A dermoscopic image of a skin lesion:
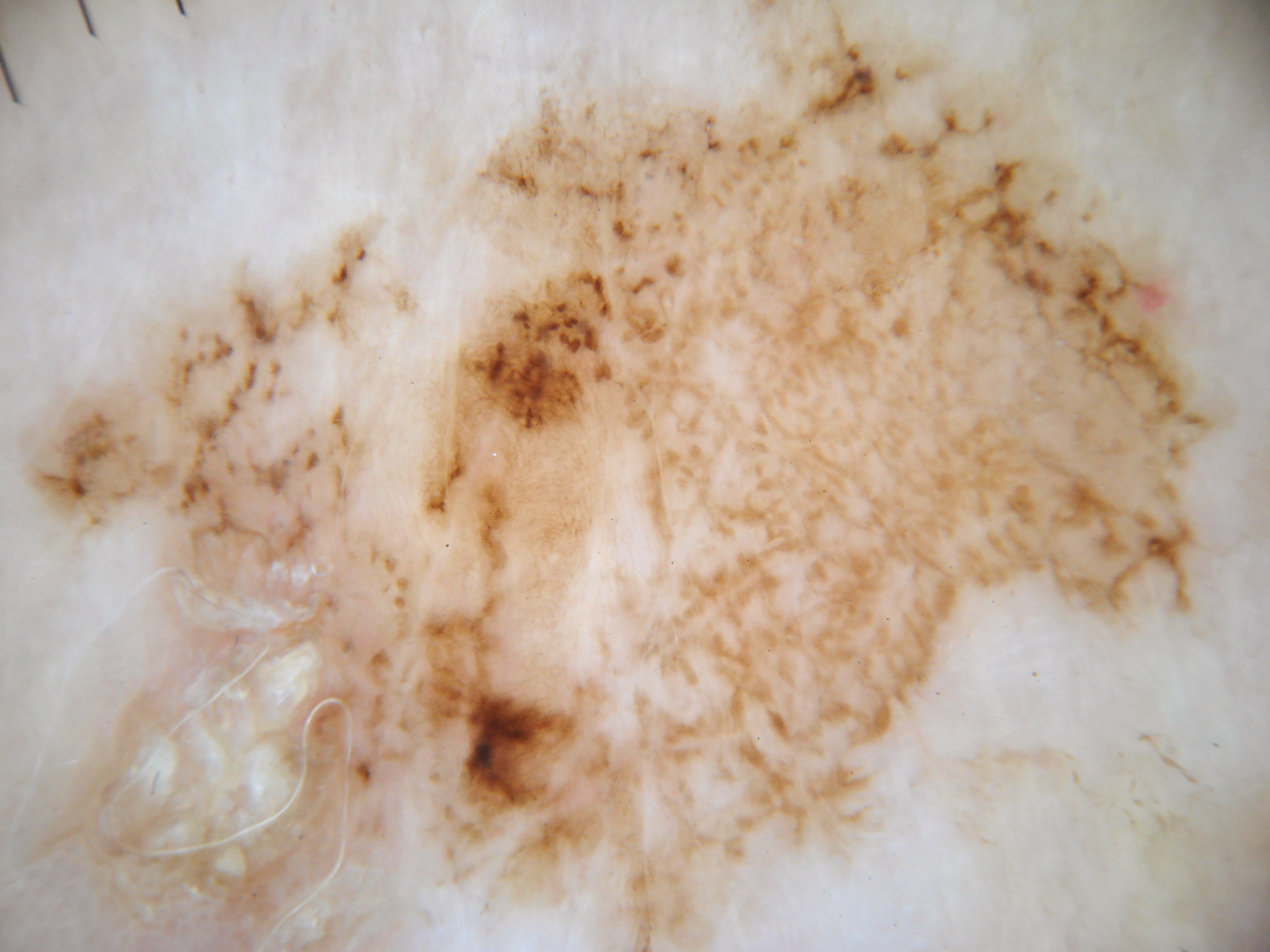The lesion stretches across essentially the whole frame. On dermoscopy, the lesion shows globules and pigment network, with no streaks, negative network, or milia-like cysts. Histopathological examination showed a melanoma, a malignancy.